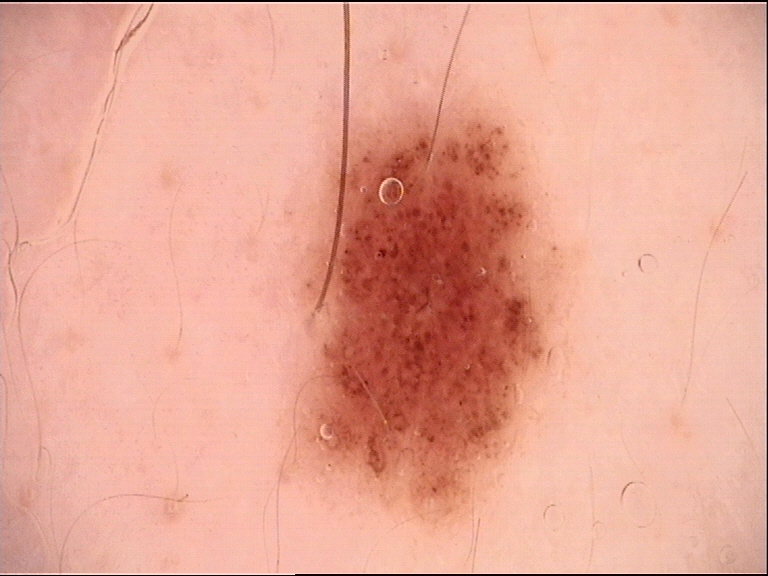Q: What is the diagnosis?
A: dysplastic junctional nevus (expert consensus)